A dermoscopic image of a skin lesion: 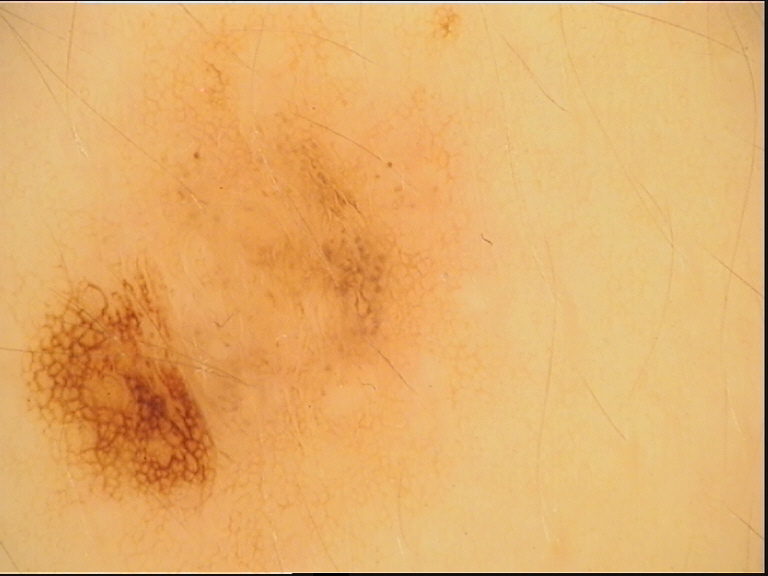Impression:
The diagnosis was a dysplastic junctional nevus.